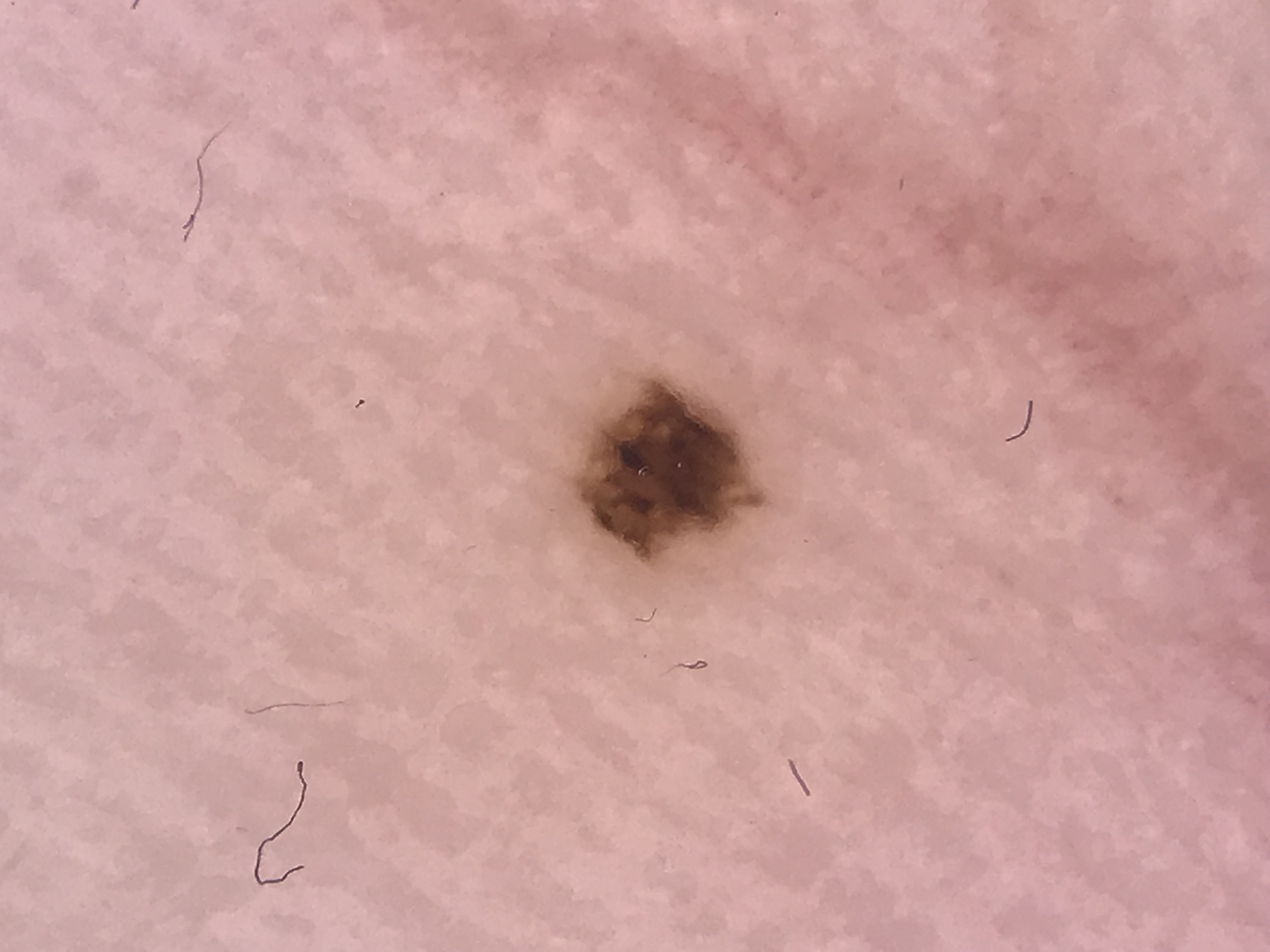<dermoscopy>
  <image>dermatoscopy</image>
  <lesion_type>
    <main_class>banal</main_class>
    <pattern>junctional</pattern>
  </lesion_type>
  <diagnosis>
    <name>acral junctional nevus</name>
    <code>ajb</code>
    <malignancy>benign</malignancy>
    <super_class>melanocytic</super_class>
    <confirmation>expert consensus</confirmation>
  </diagnosis>
</dermoscopy>